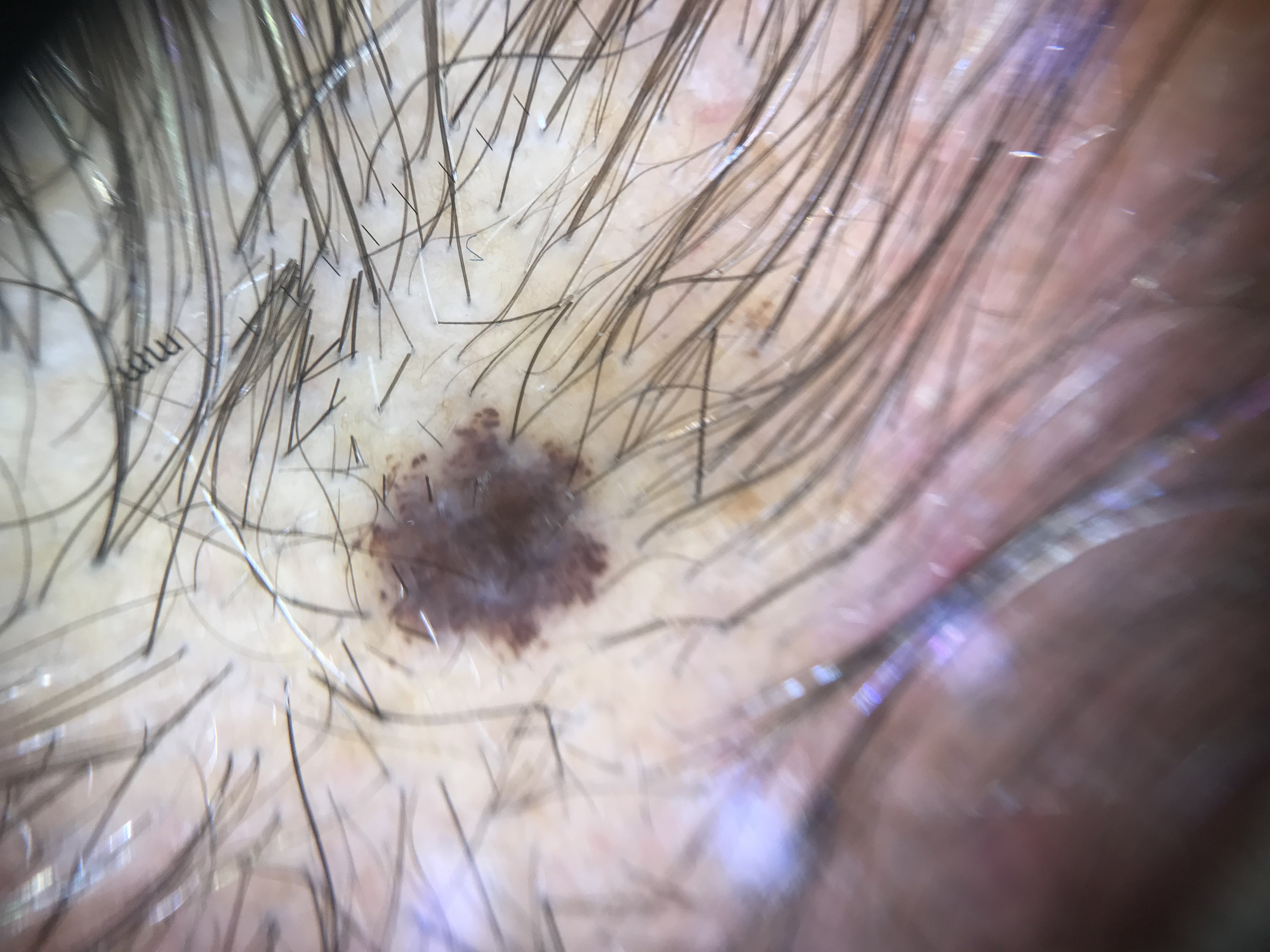image — dermoscopy; label — dysplastic compound nevus (expert consensus).